This image was taken at an angle — 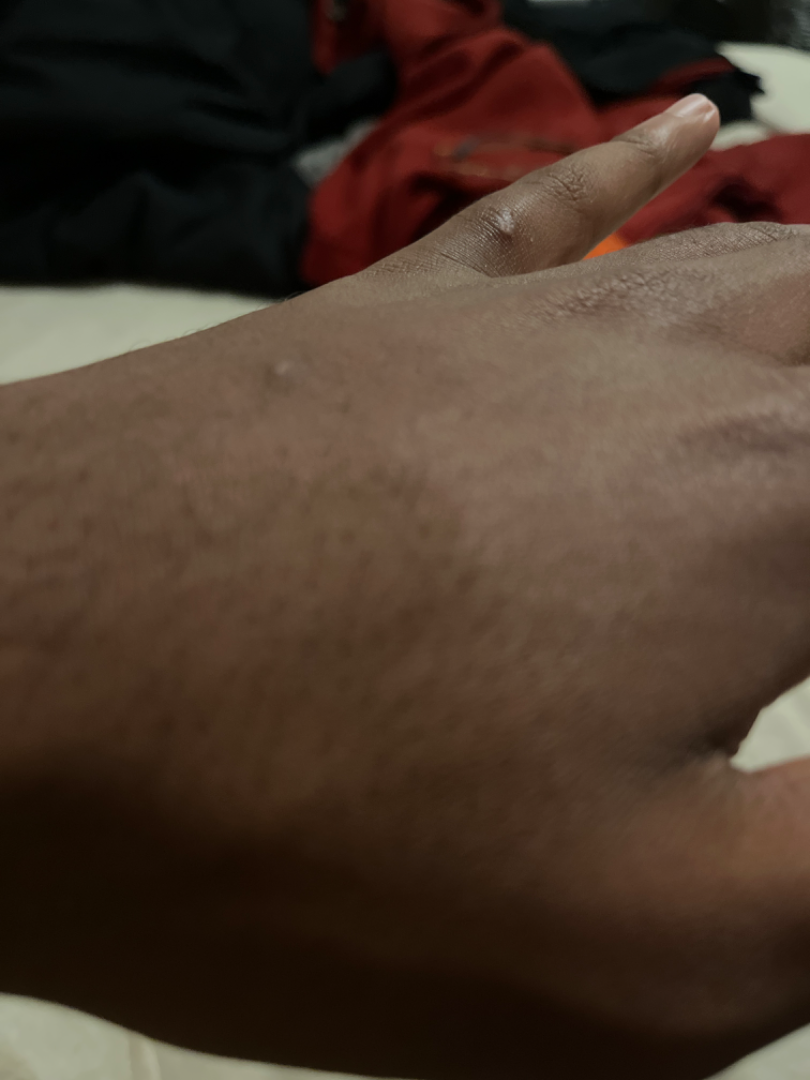Review: On dermatologist assessment of the image, the favored diagnosis is Prurigo nodularis; also on the differential is Calcinosis cutis.